A close-up photograph. The palm and back of the hand are involved. The subject is 50–59, female.
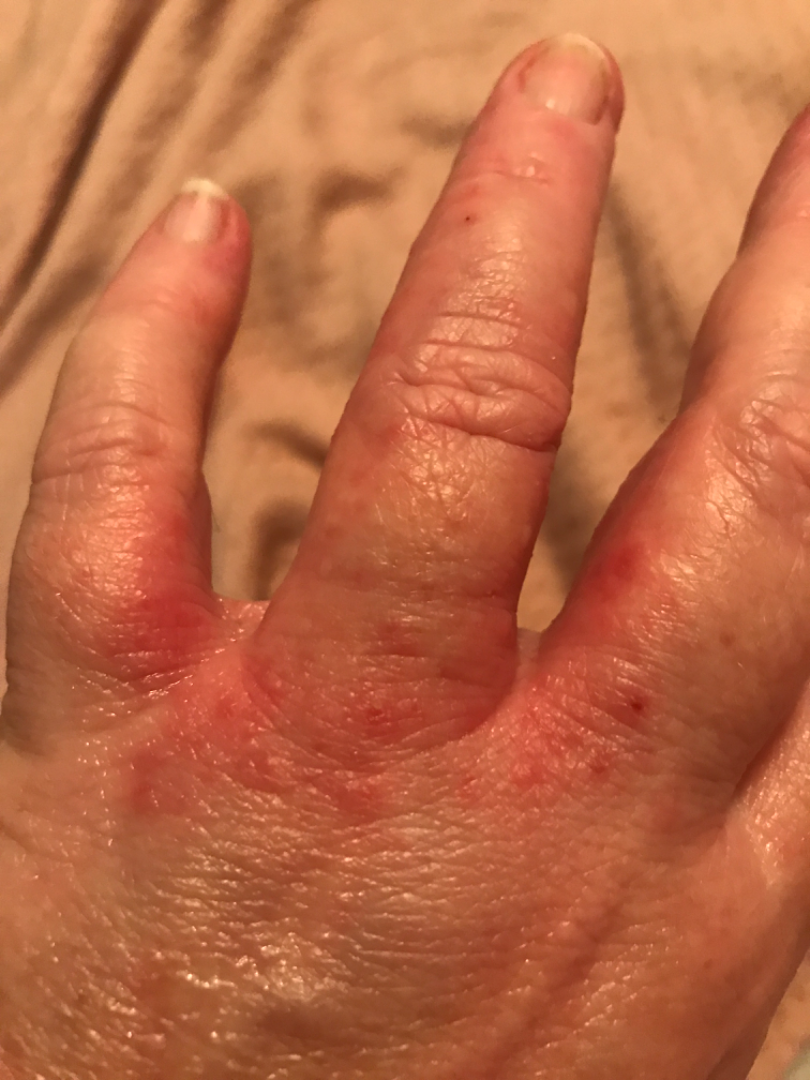Present for more than one year.
The contributor reports itching, bothersome appearance and enlargement.
Texture is reported as rough or flaky and raised or bumpy.
Eczema (favored); Allergic Contact Dermatitis (considered); Scabies (remote); Tinea (remote); Irritant Contact Dermatitis (remote).